A dermoscopic close-up of a skin lesion: 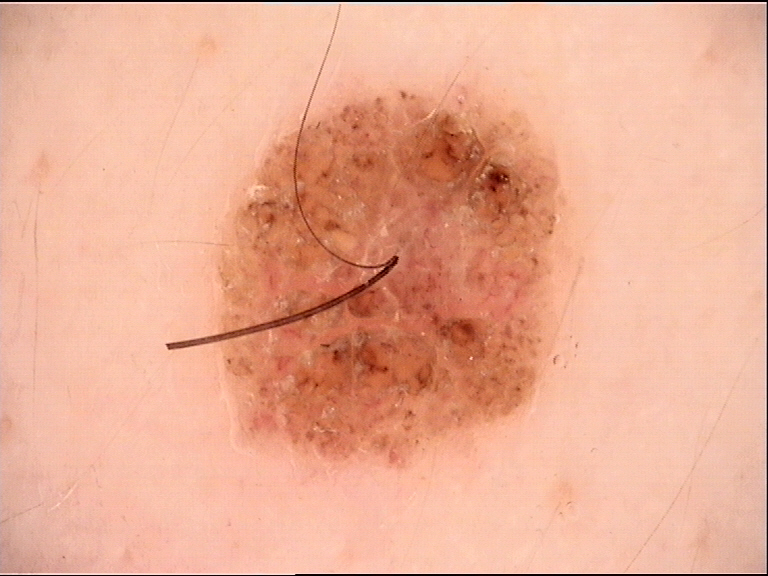Consistent with a banal lesion — a dermal nevus.